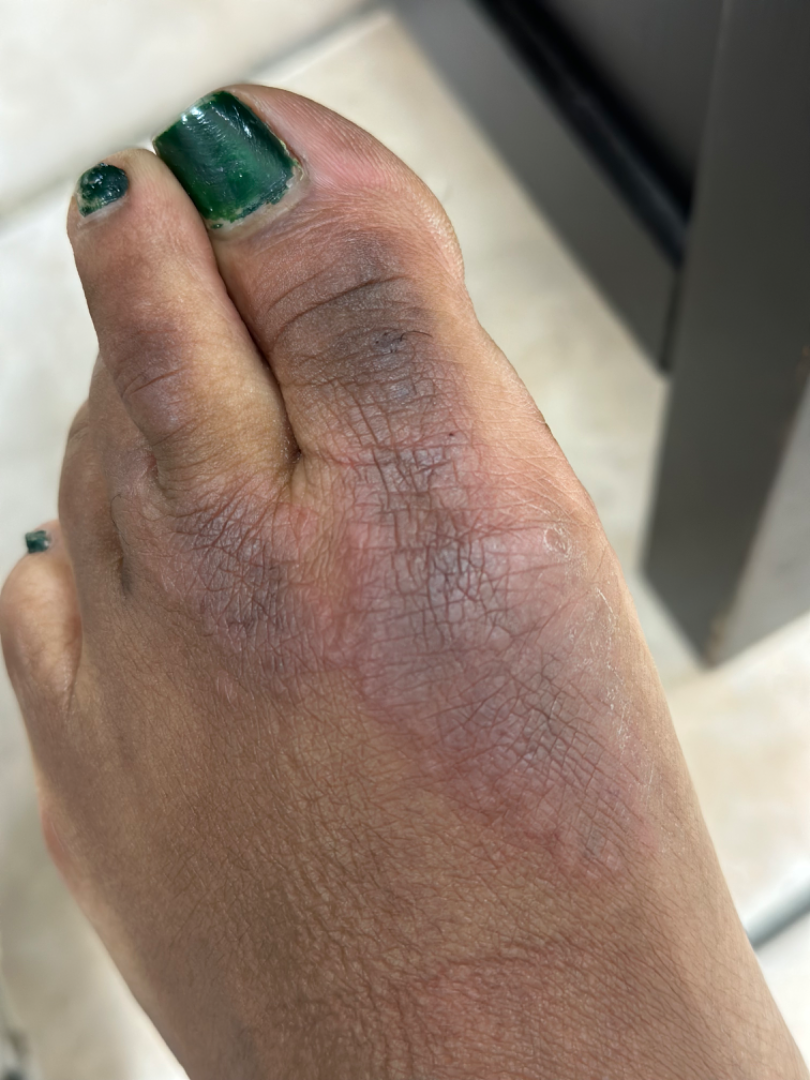The reviewer was unable to grade this case for skin condition.
This image was taken at an angle.
The affected area is the back of the hand and top or side of the foot.
Female patient, age 18–29.